This image was taken at a distance — 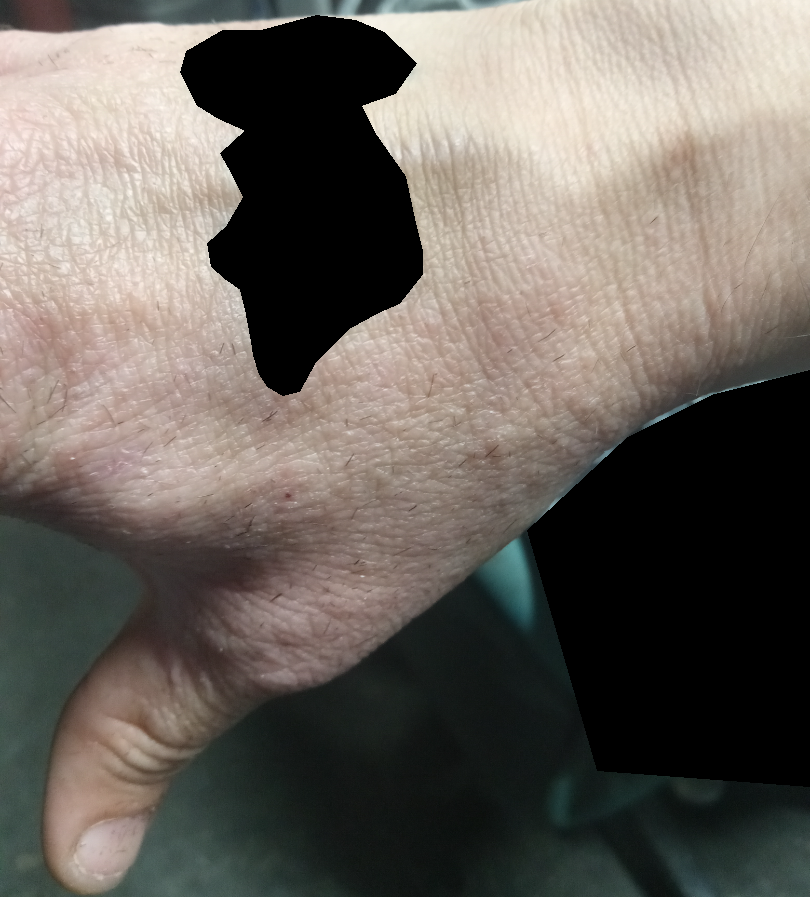Review: The reviewing dermatologist was unable to assign a differential diagnosis from the image.